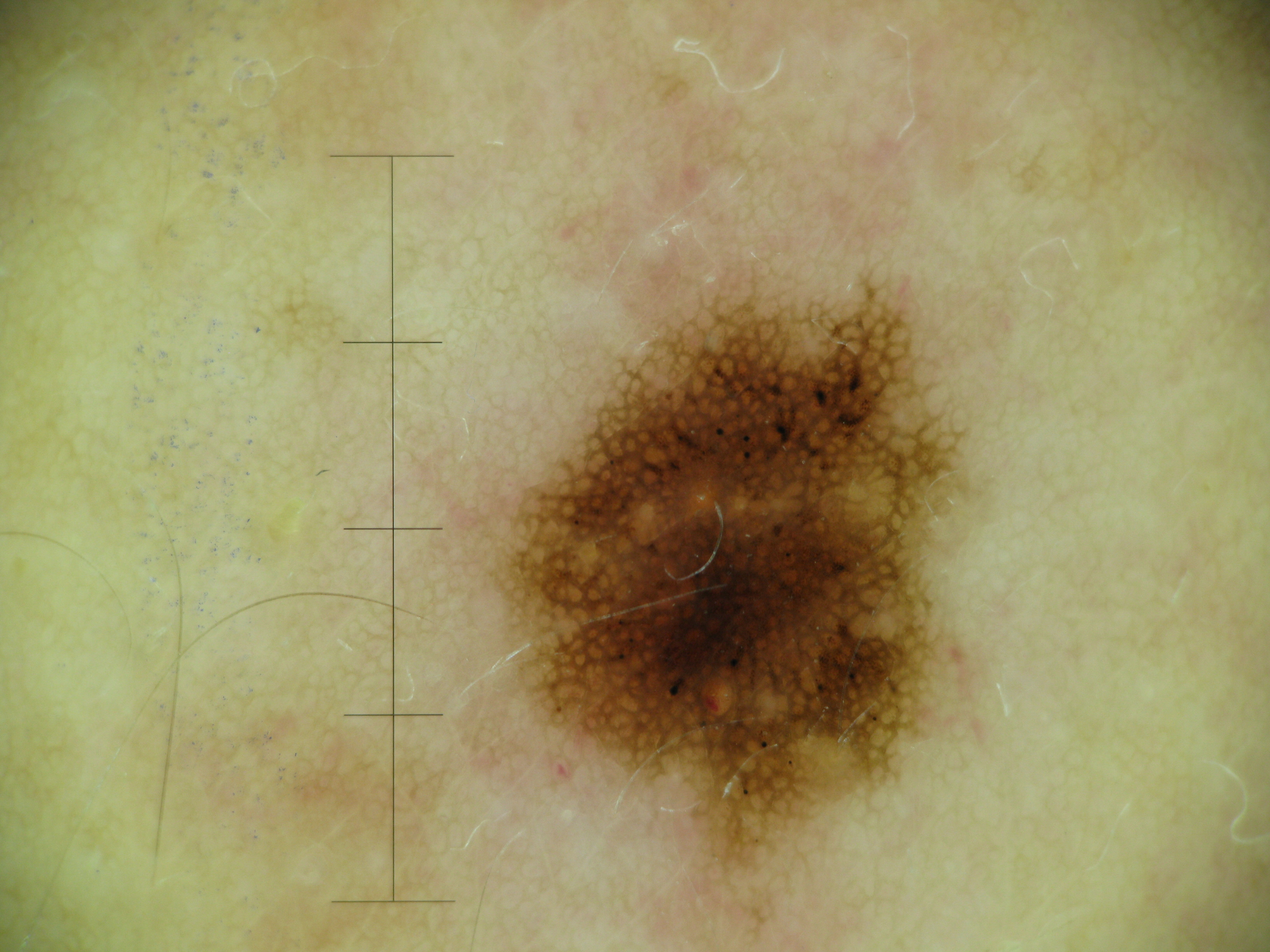diagnostic label — dysplastic junctional nevus (expert consensus).